Reported duration is about one day. Skin tone: Fitzpatrick phototype III. The photograph was taken at an angle. The contributor reports itching, enlargement, burning and pain. The lesion involves the leg. The patient considered this a rash.
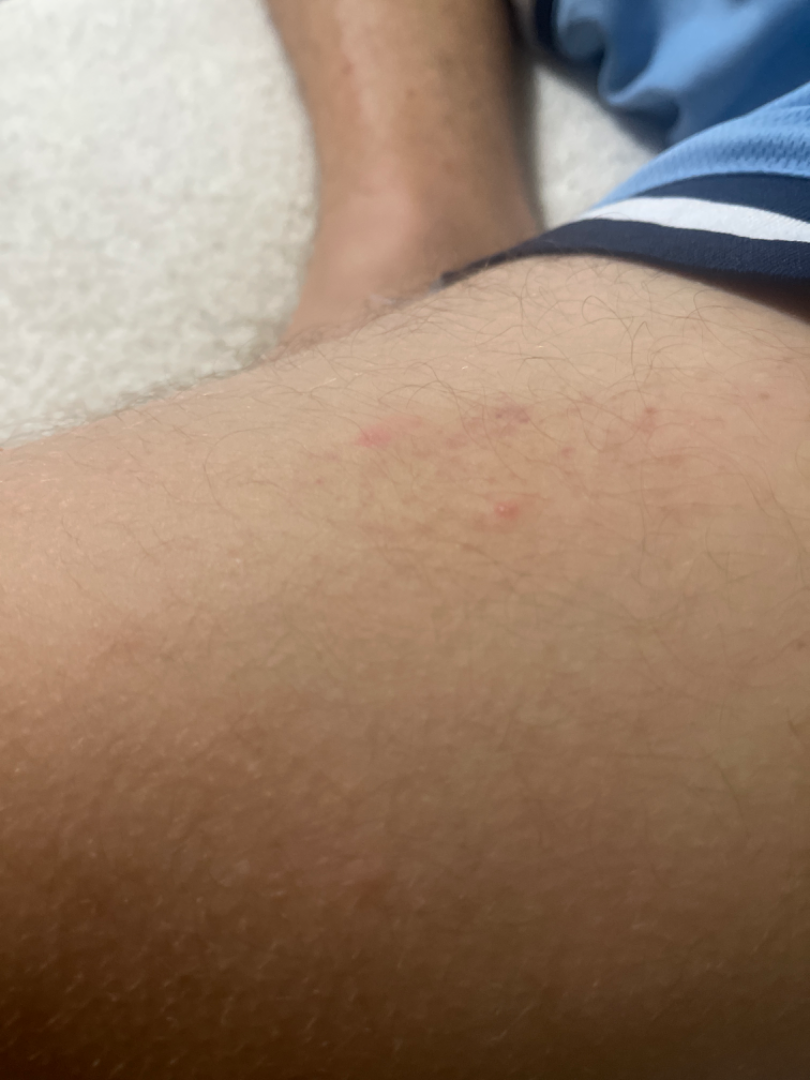differential diagnosis: Folliculitis, ecchymoses and Post-Inflammatory hyperpigmentation were considered with similar weight